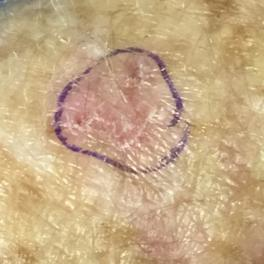Summary:
A patient in their early 70s. A smartphone photograph of a skin lesion. The lesion is located on a forearm. By the patient's account, the lesion itches, but has not changed and has not grown.
Conclusion:
The diagnostic impression was an actinic keratosis.